A dermoscopic image of a skin lesion.
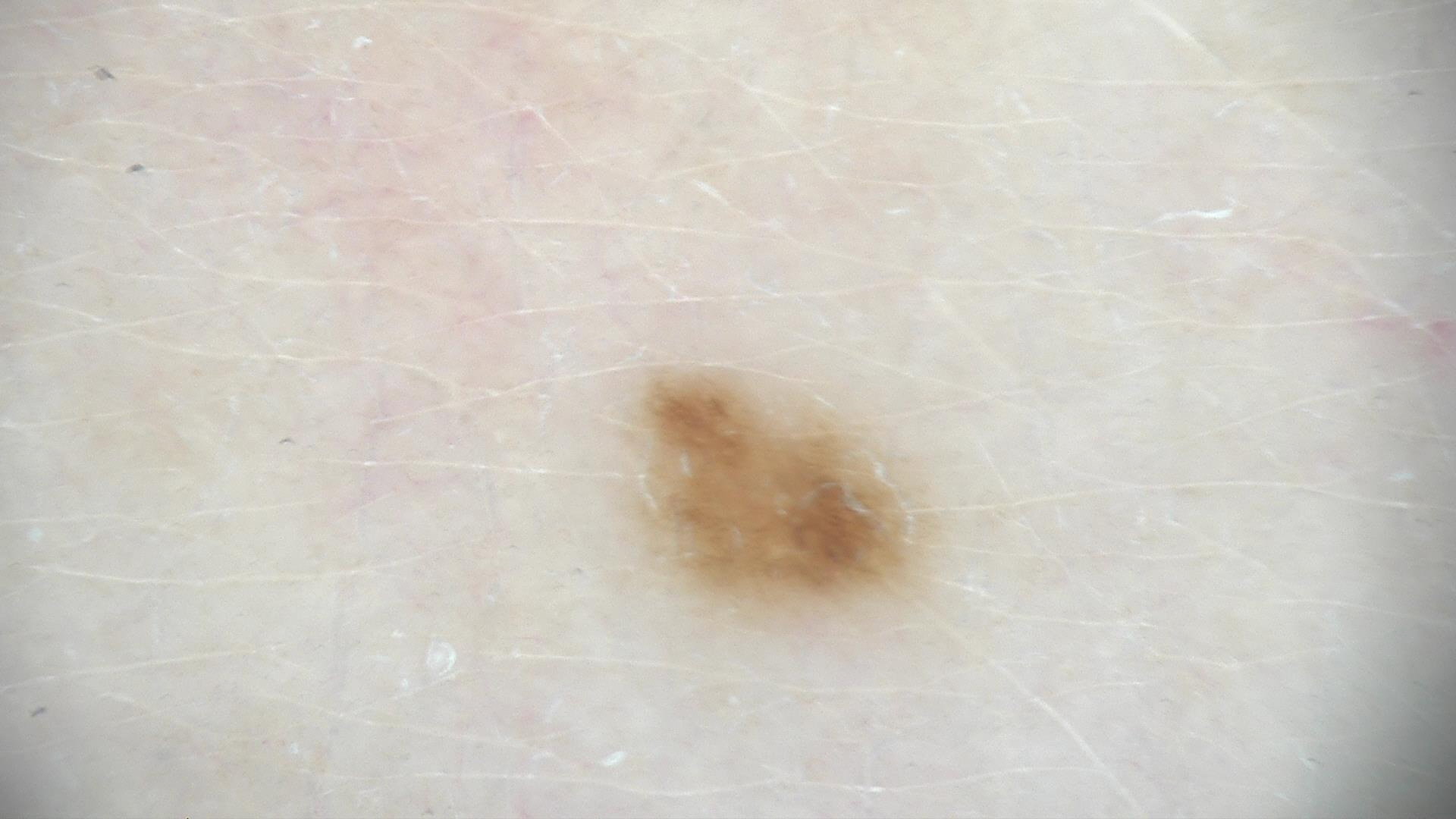The diagnosis was a dysplastic junctional nevus.